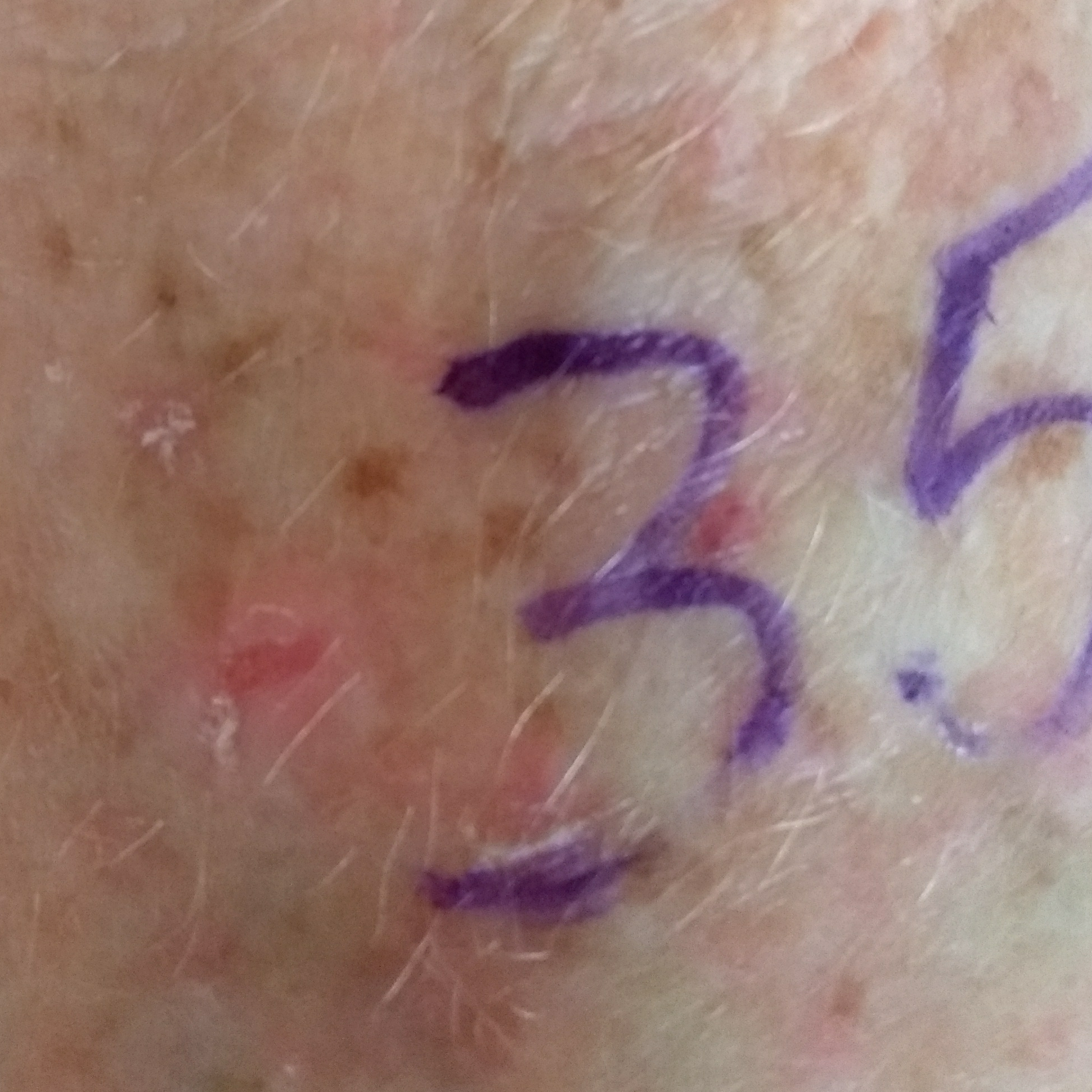The consensus clinical diagnosis was an actinic keratosis.